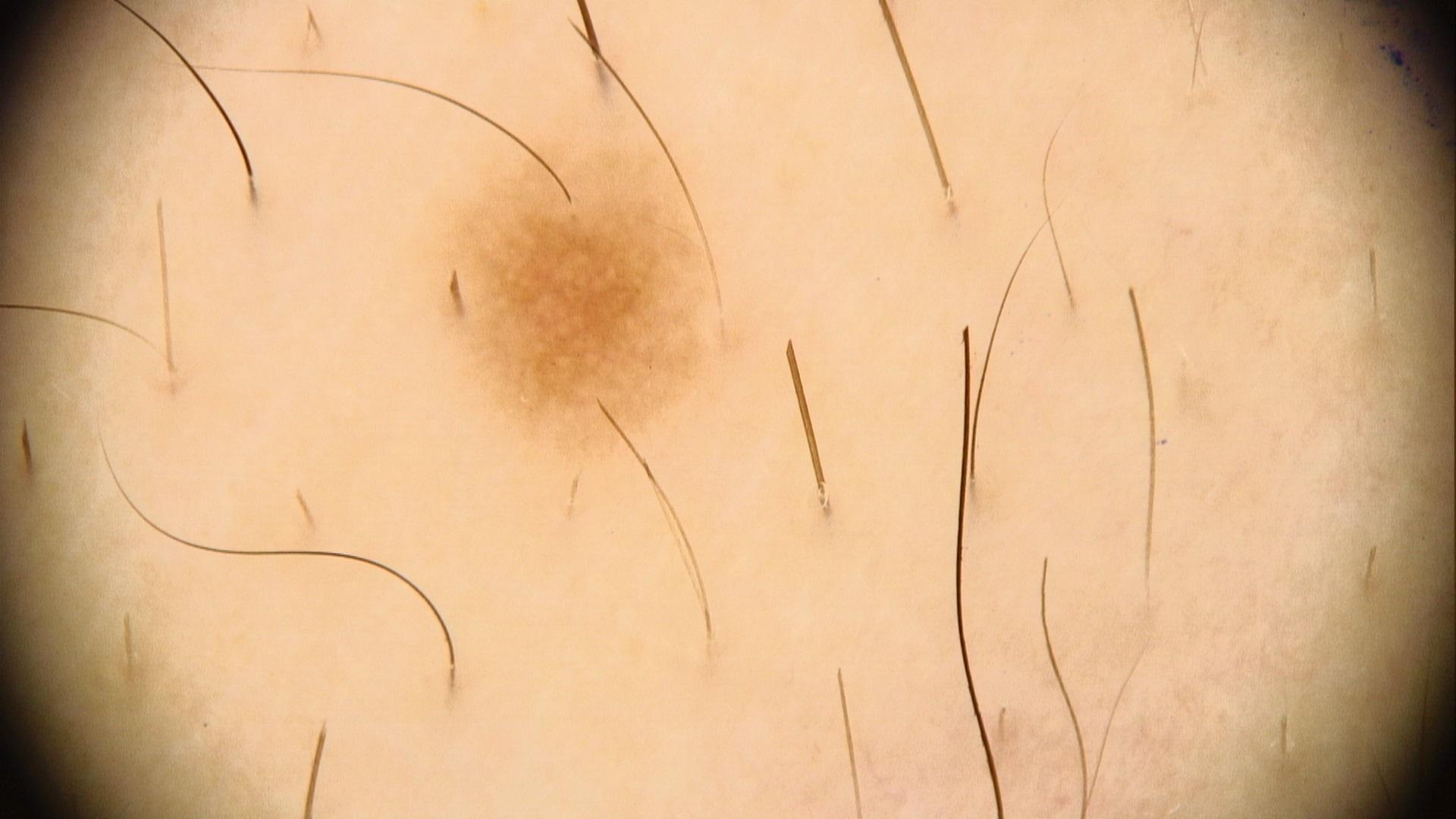A dermoscopic image of a skin lesion. A male patient aged 18-22. The lesion is on an upper extremity. The clinical impression was a benign, melanocytic lesion — a nevus.